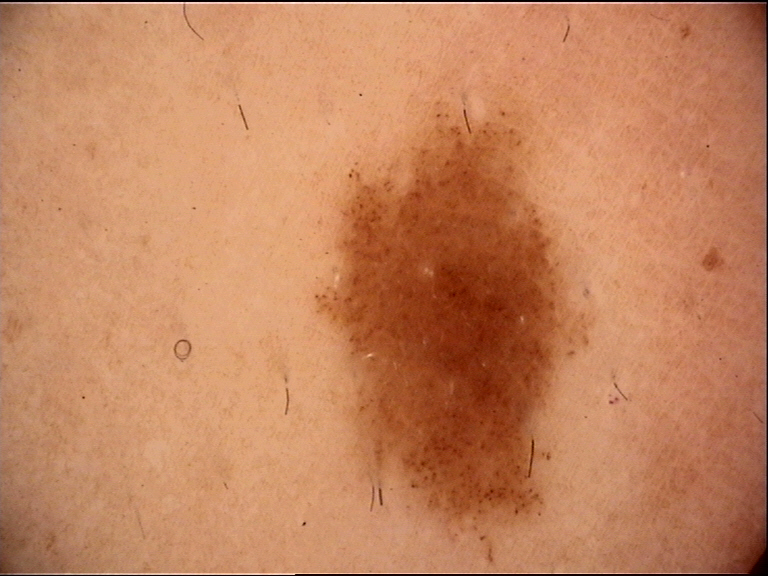Case:
A skin lesion imaged with a dermatoscope.
Impression:
The diagnosis was a banal lesion — a junctional nevus.